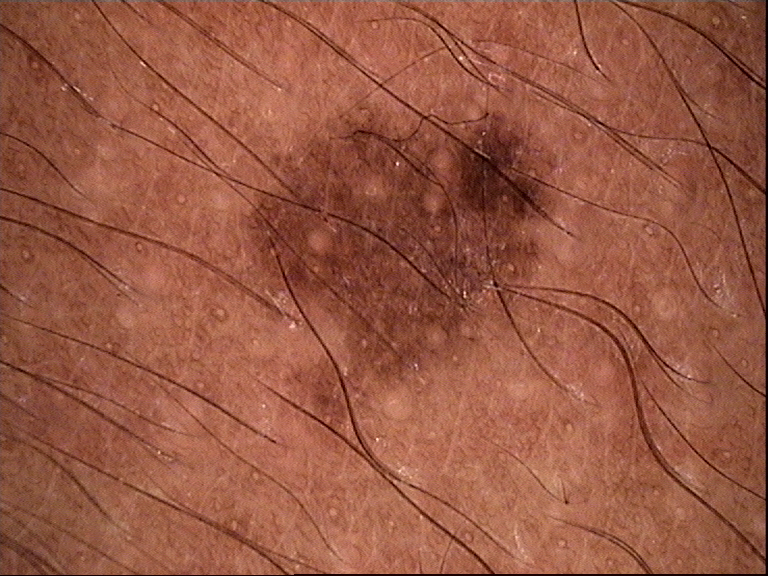A dermoscopic photograph of a skin lesion. Consistent with a dysplastic junctional nevus.